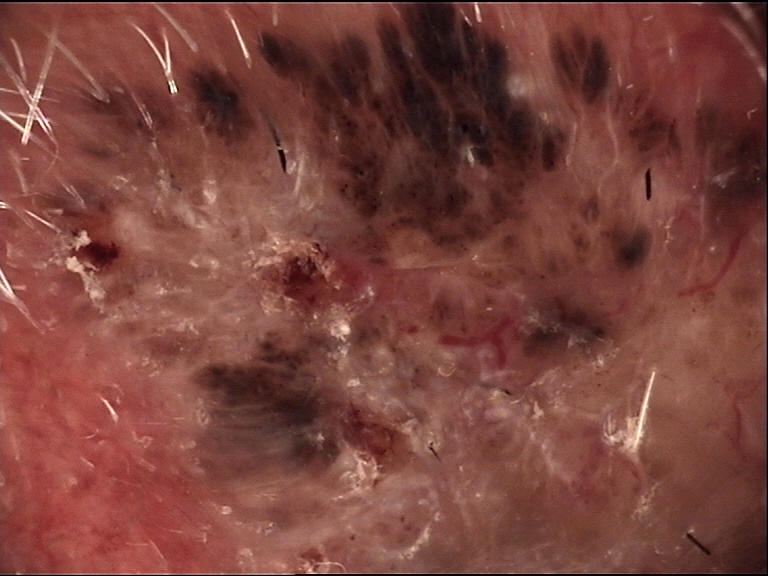Case:
Dermoscopy of a skin lesion.
Pathology:
The biopsy diagnosis was a keratinocytic lesion — a basal cell carcinoma.